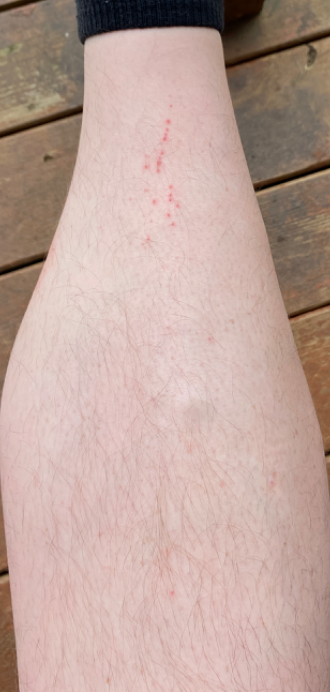Findings:
* assessment: indeterminate from the photograph
* texture: flat
* reported symptoms: itching
* patient: male, age 18–29
* symptom duration: about one day
* self-categorized as: a rash
* framing: at a distance
* body site: leg